A dermatoscopic image of a skin lesion:
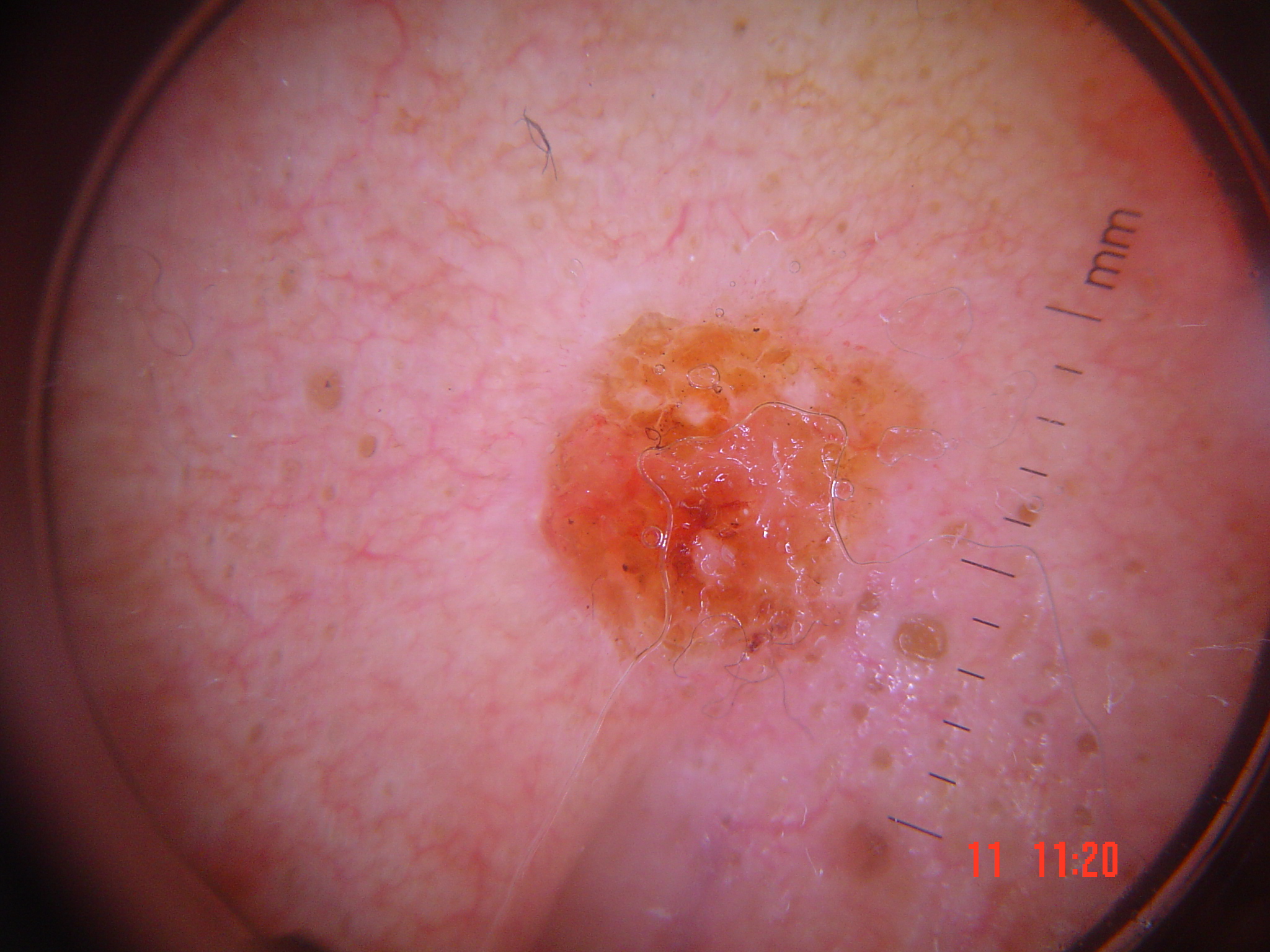{
  "lesion_type": {
    "main_class": "keratinocytic"
  },
  "diagnosis": {
    "name": "squamous cell carcinoma",
    "code": "scc",
    "malignancy": "malignant",
    "super_class": "non-melanocytic",
    "confirmation": "histopathology"
  }
}